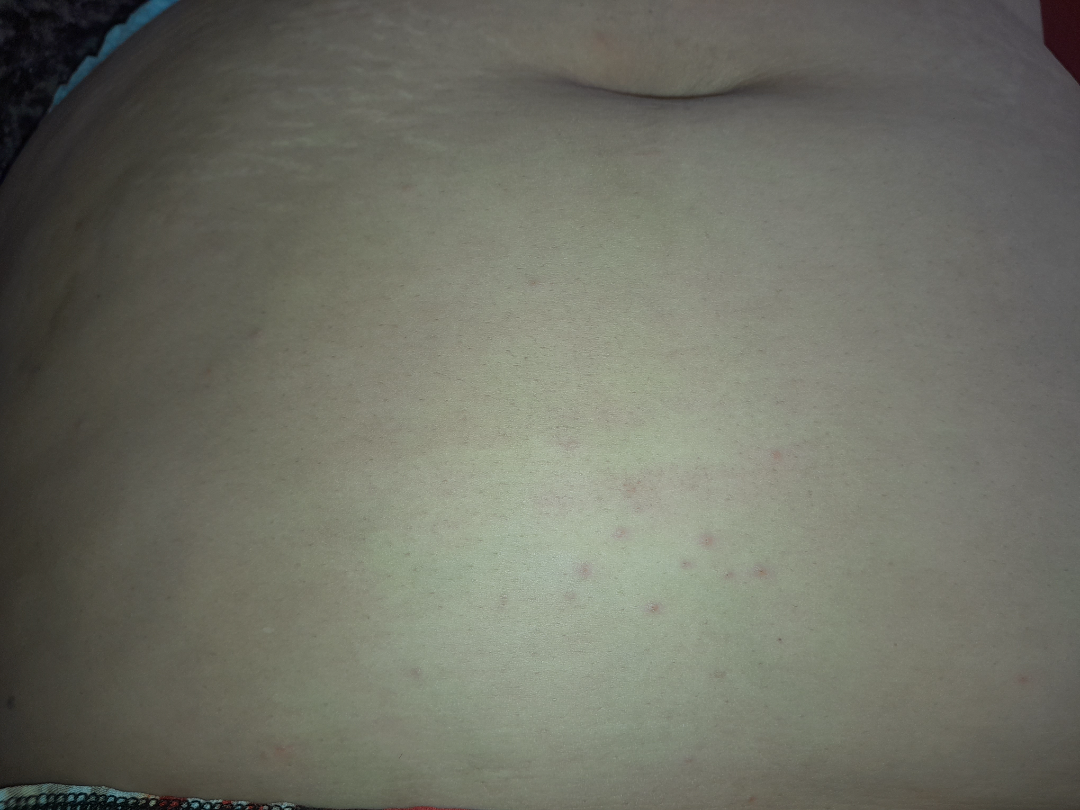Located on the front of the torso. An image taken at a distance. Folliculitis (considered); Molluscum Contagiosum (considered); Scabies (less likely).